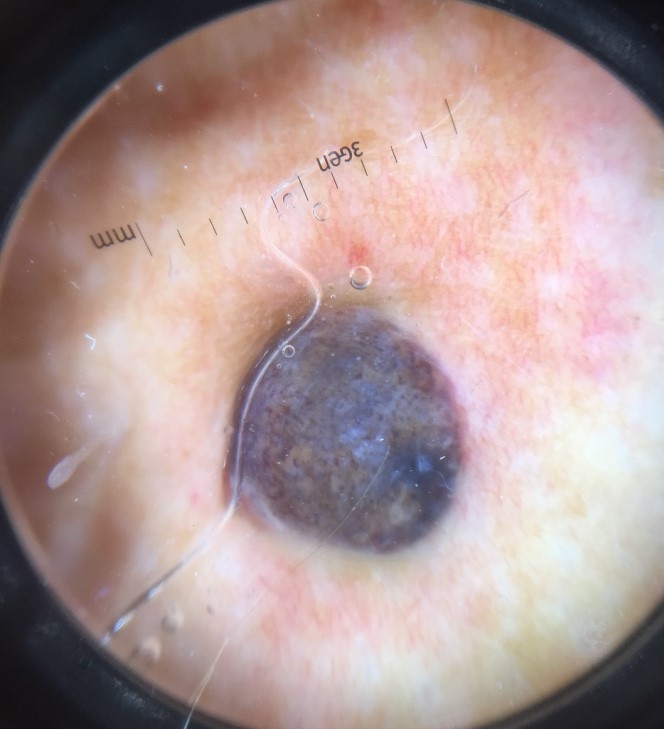modality: dermoscopy, diagnosis: melanoma (biopsy-proven).